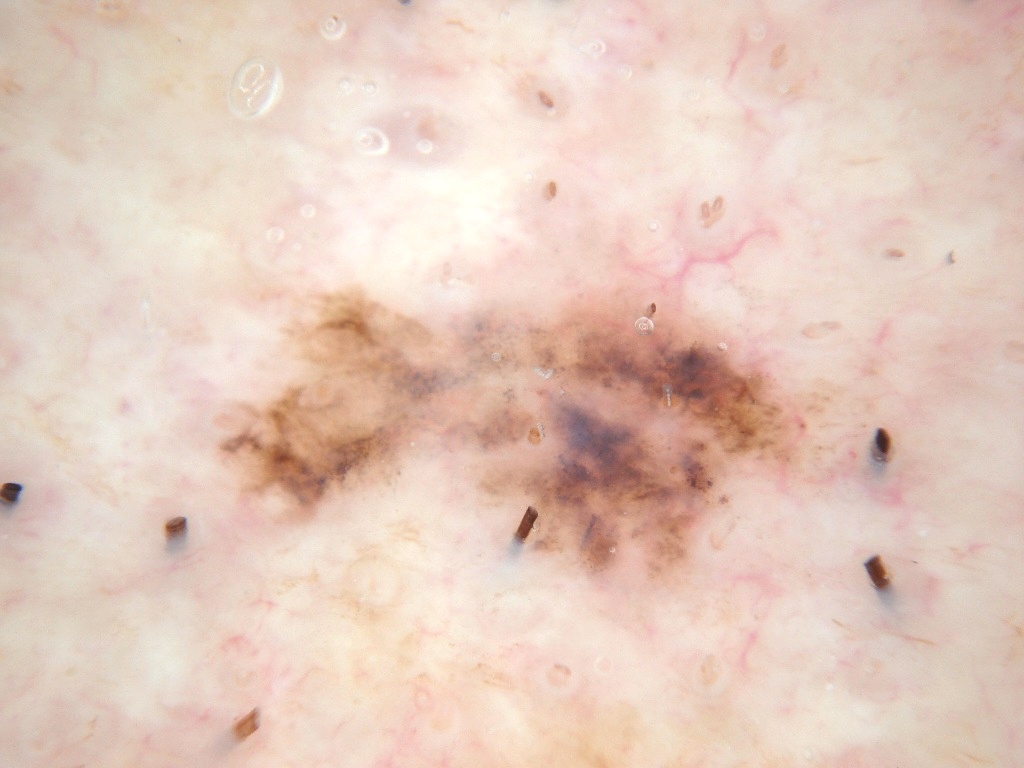A male patient, roughly 75 years of age.
A dermoscopic view of a skin lesion.
As (left, top, right, bottom), the lesion spans 195 272 887 616.
Dermoscopic assessment notes no milia-like cysts, pigment network, negative network, streaks, or globules.
On biopsy, the diagnosis was a melanoma, a skin cancer.